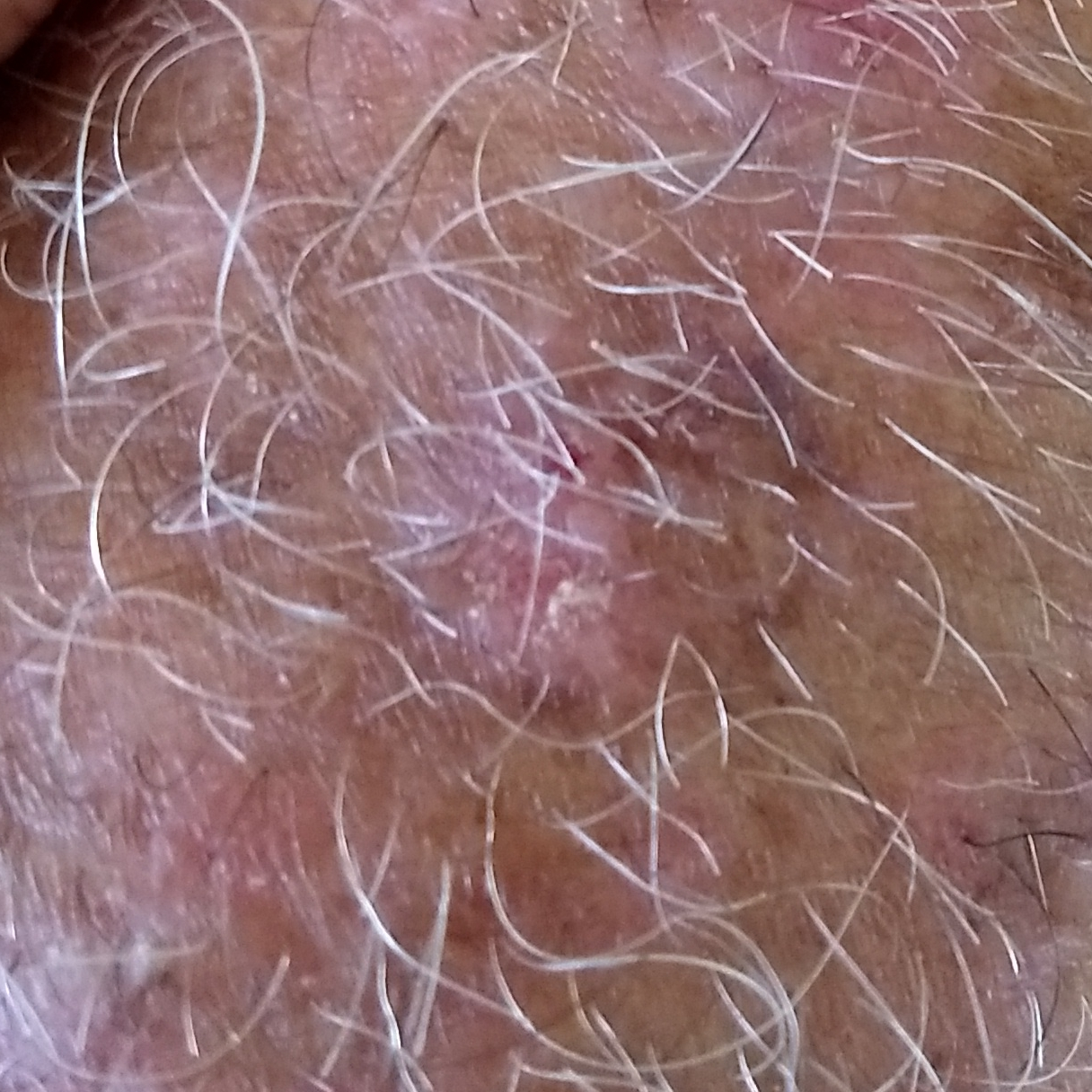A clinical photograph of a skin lesion. A male subject 81 years old. The lesion is located on an arm. The lesion measures 10 × 9 mm. No symptoms reported. The diagnostic impression was an actinic keratosis.